Skin tone: Fitzpatrick phototype II. The contributor notes the lesion is raised or bumpy. This image was taken at an angle. The arm is involved. The patient described the issue as a rash. The condition has been present for less than one week. Reported lesion symptoms include bothersome appearance and itching. Male subject, age 18–29: 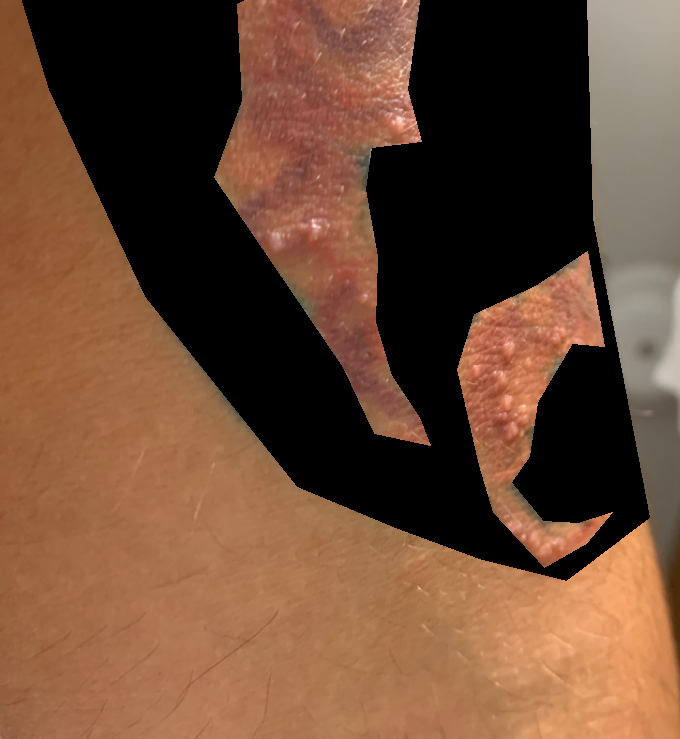Findings: The reviewing dermatologists' impression was: most consistent with Skin infection; also consider Foreign body reaction of the skin.